A dermatoscopic image of a skin lesion: 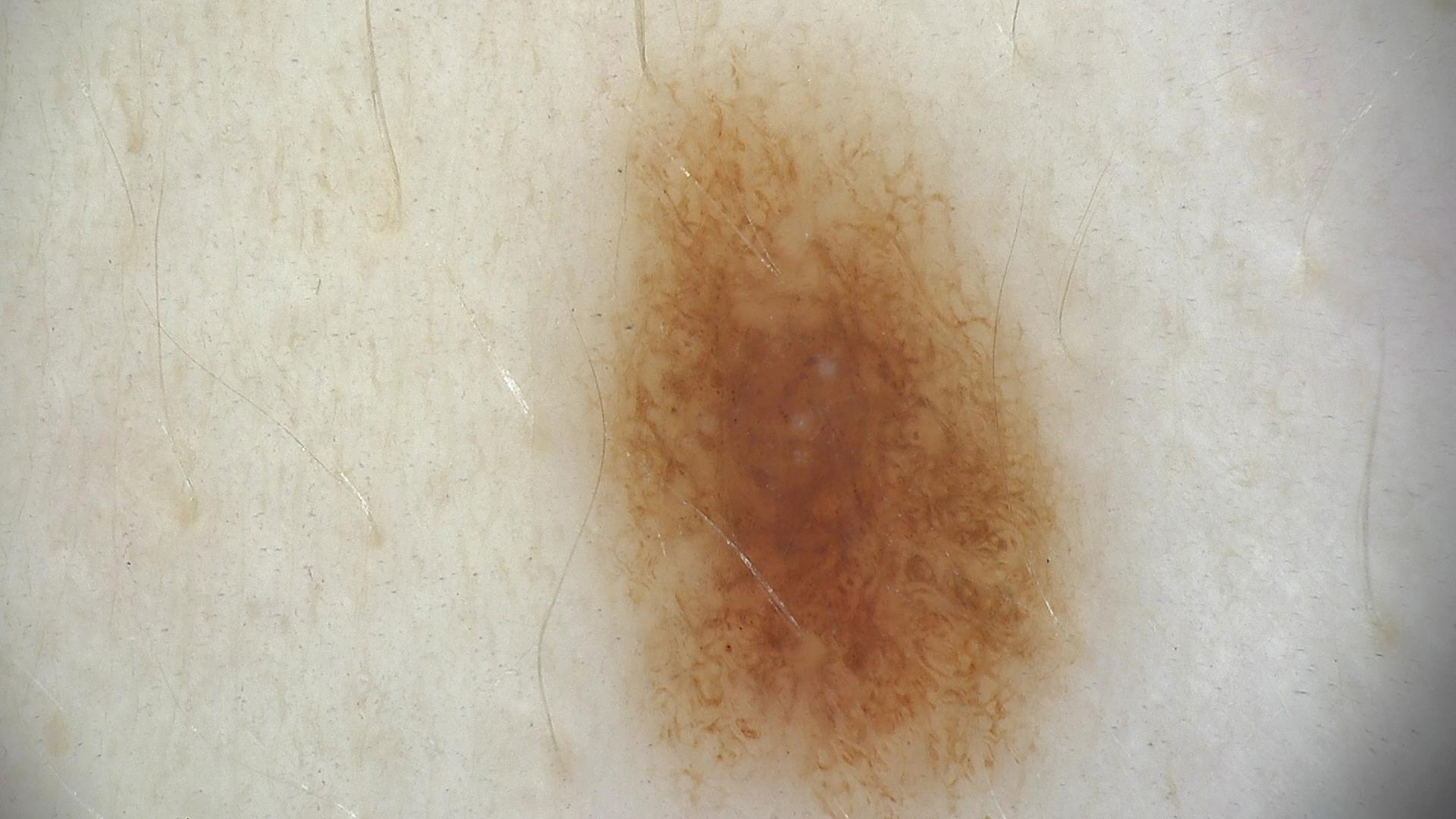Conclusion: The diagnosis was a benign lesion — a dysplastic junctional nevus.